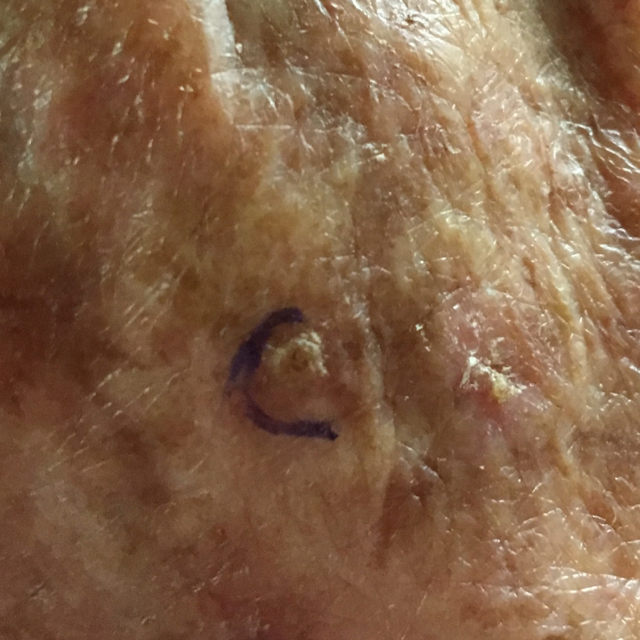Expert review favored an actinic keratosis.